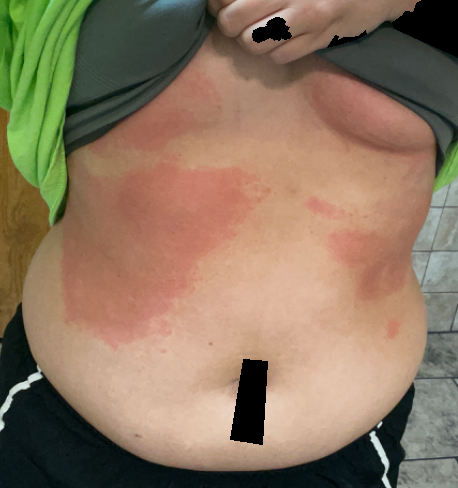The reviewer was unable to grade this case for skin condition. The photo was captured at a distance.